The photo was captured at an angle.
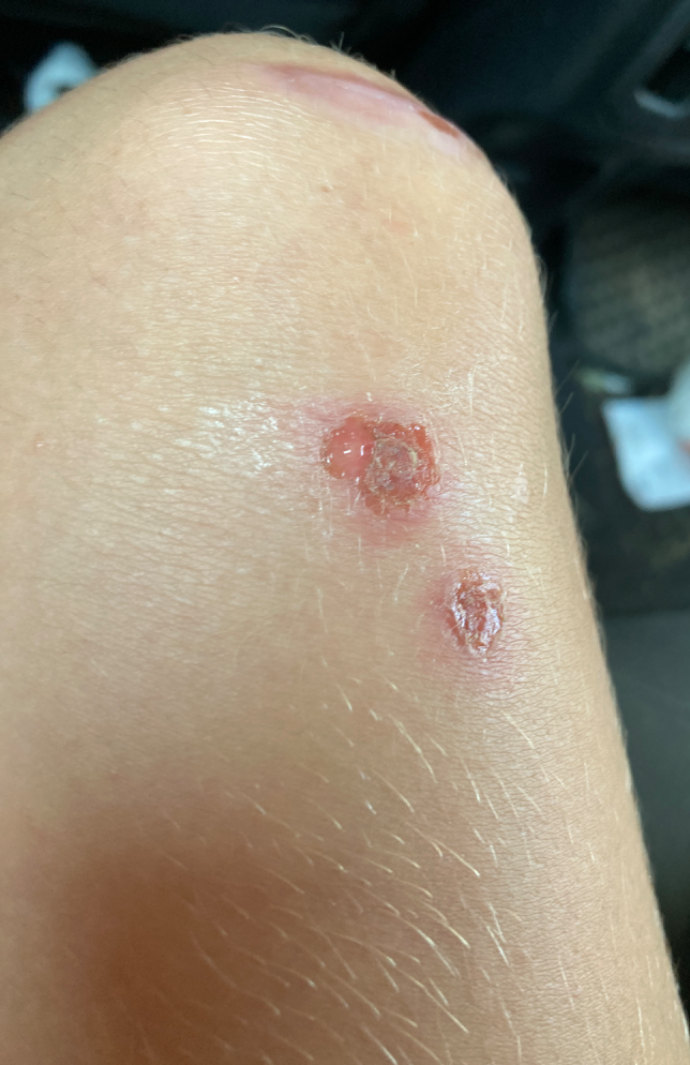Impression: The reviewing dermatologist's impression was: the differential is split between Ecthyma and Impetigo.